A wide-field clinical photograph of a skin lesion. Recorded as FST II. A male patient roughly 75 years of age — 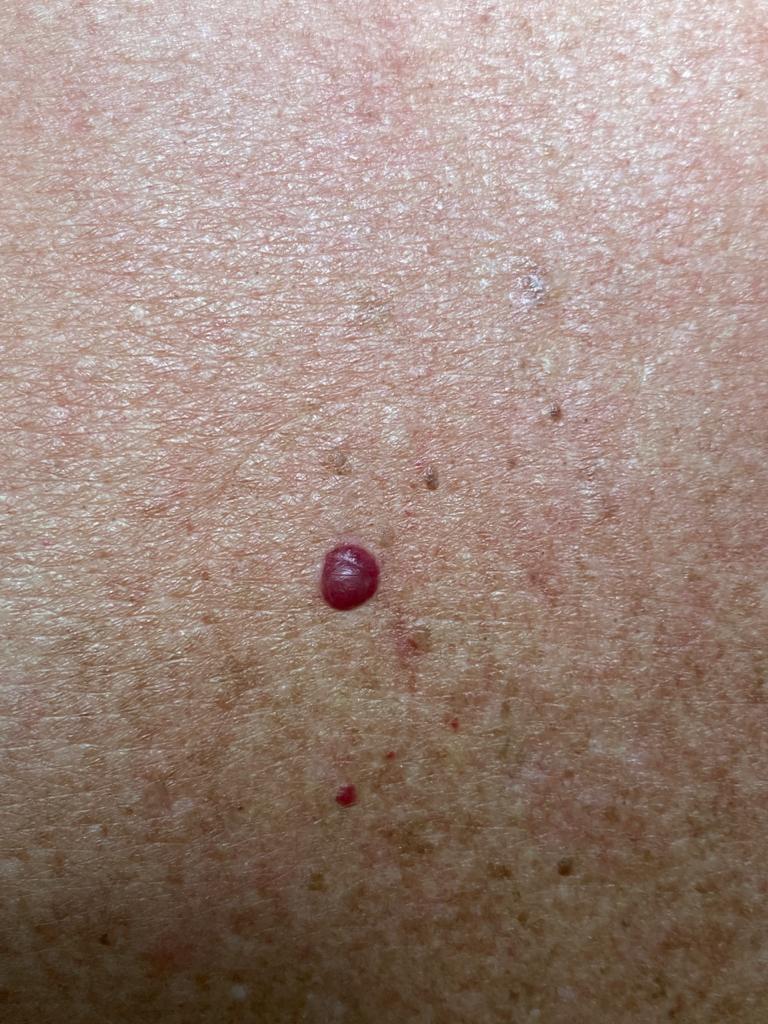Q: What is the anatomic site?
A: the trunk, specifically the anterior trunk
Q: What is this lesion?
A: vascular lesion (clinical impression)